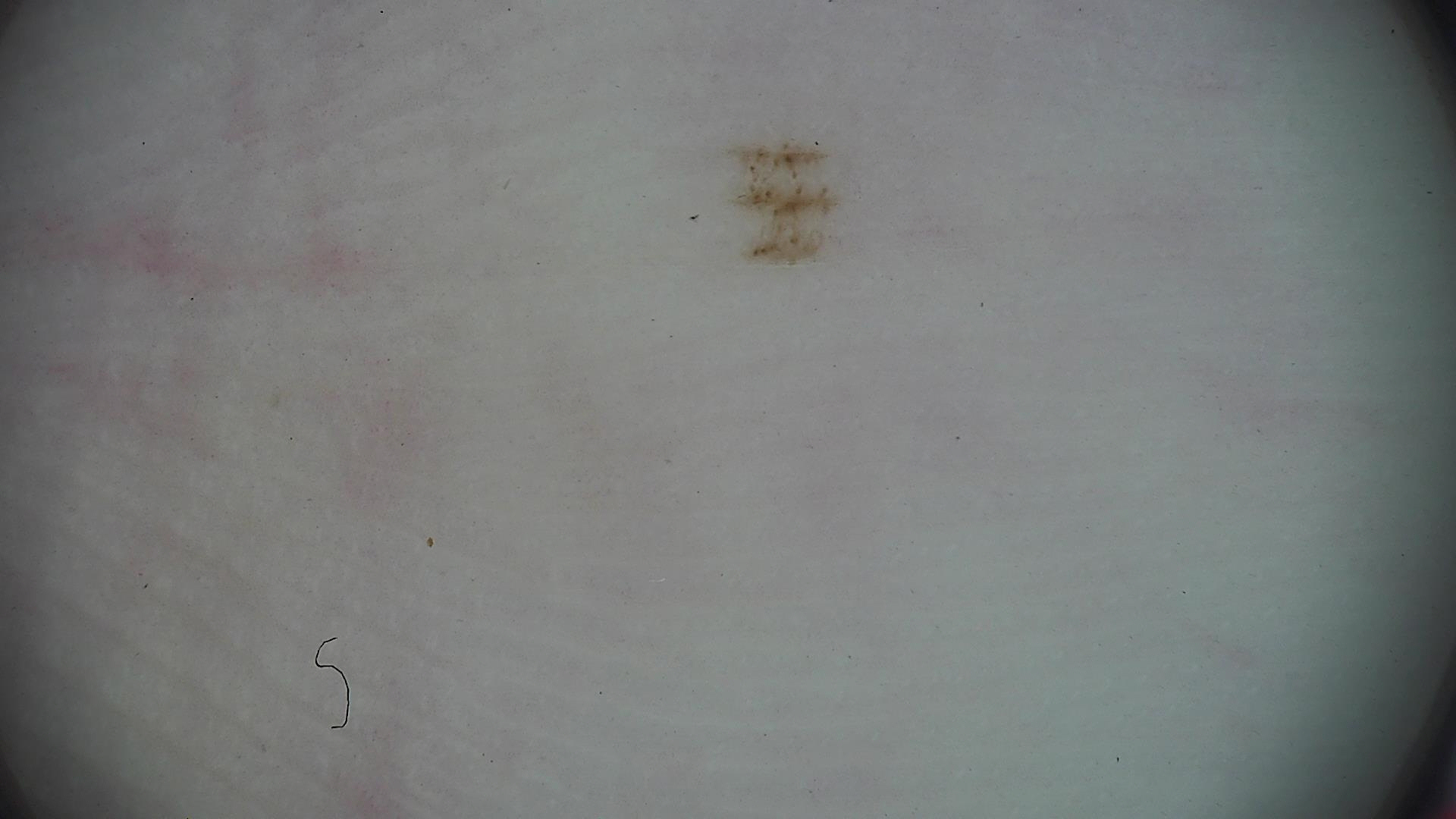A dermoscopic close-up of a skin lesion. Labeled as an acral dysplastic junctional nevus.